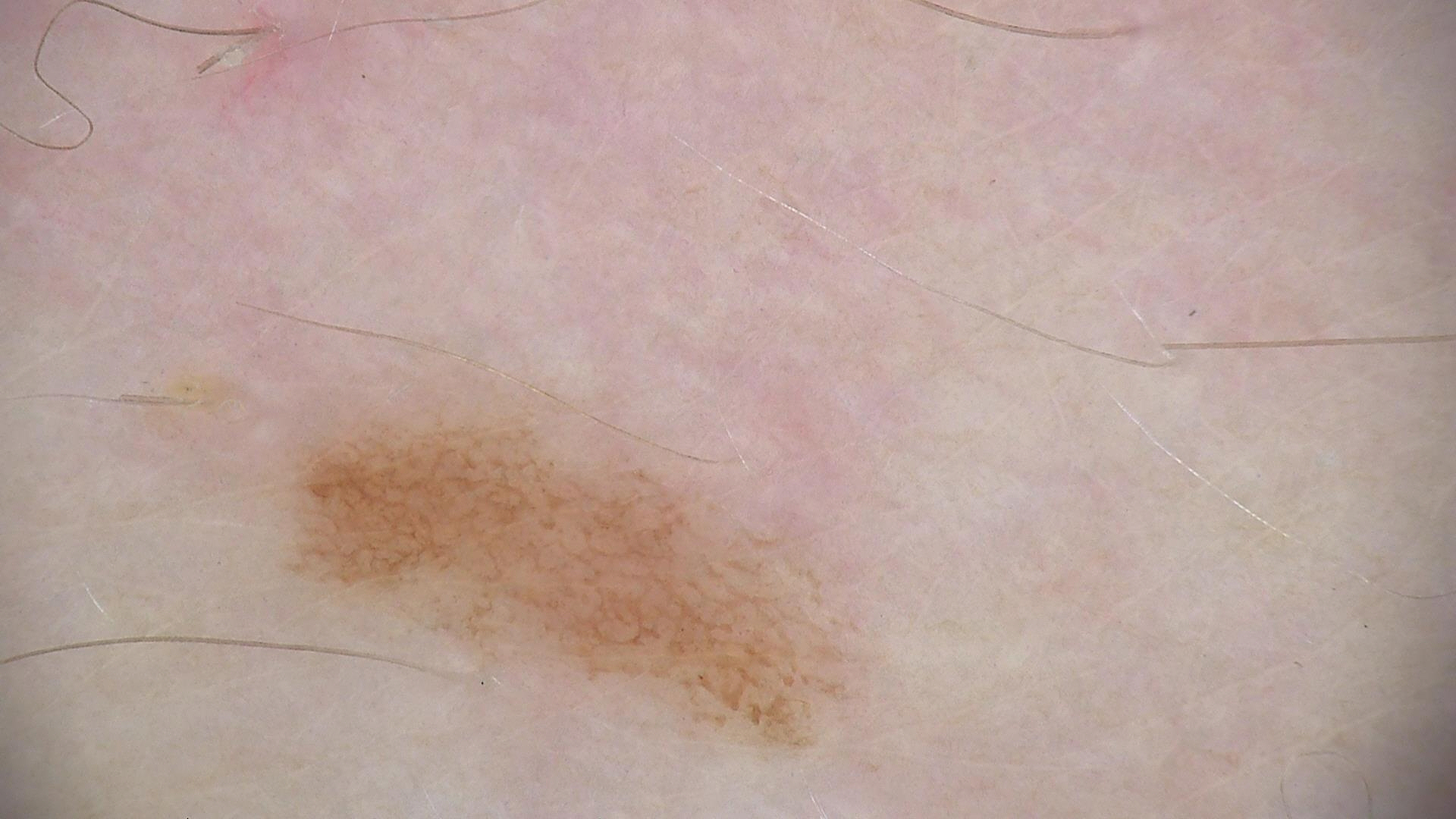– assessment · junctional nevus (expert consensus)